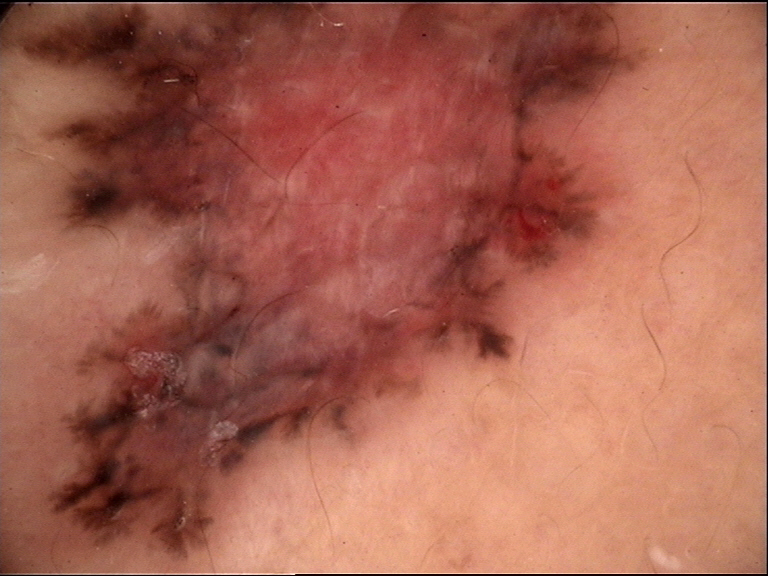Pathology: The biopsy diagnosis was a basal cell carcinoma.